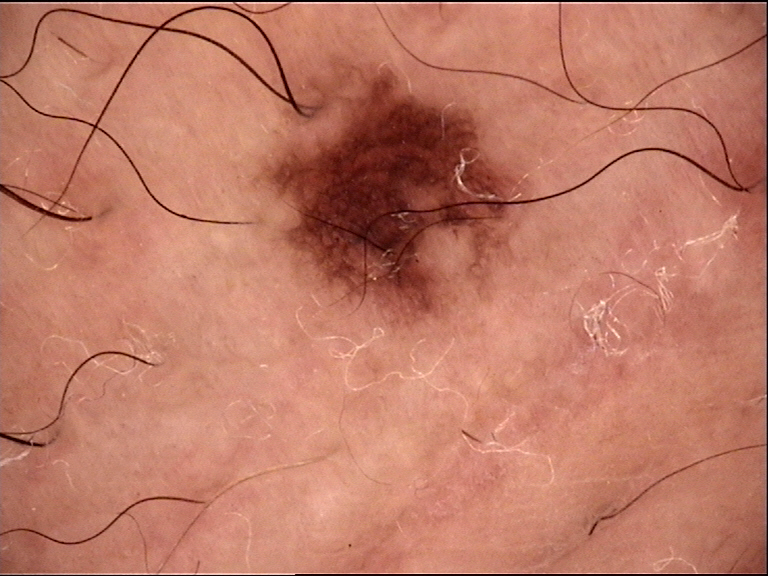Dermoscopy of a skin lesion. The architecture is that of a banal lesion. Labeled as a compound nevus.